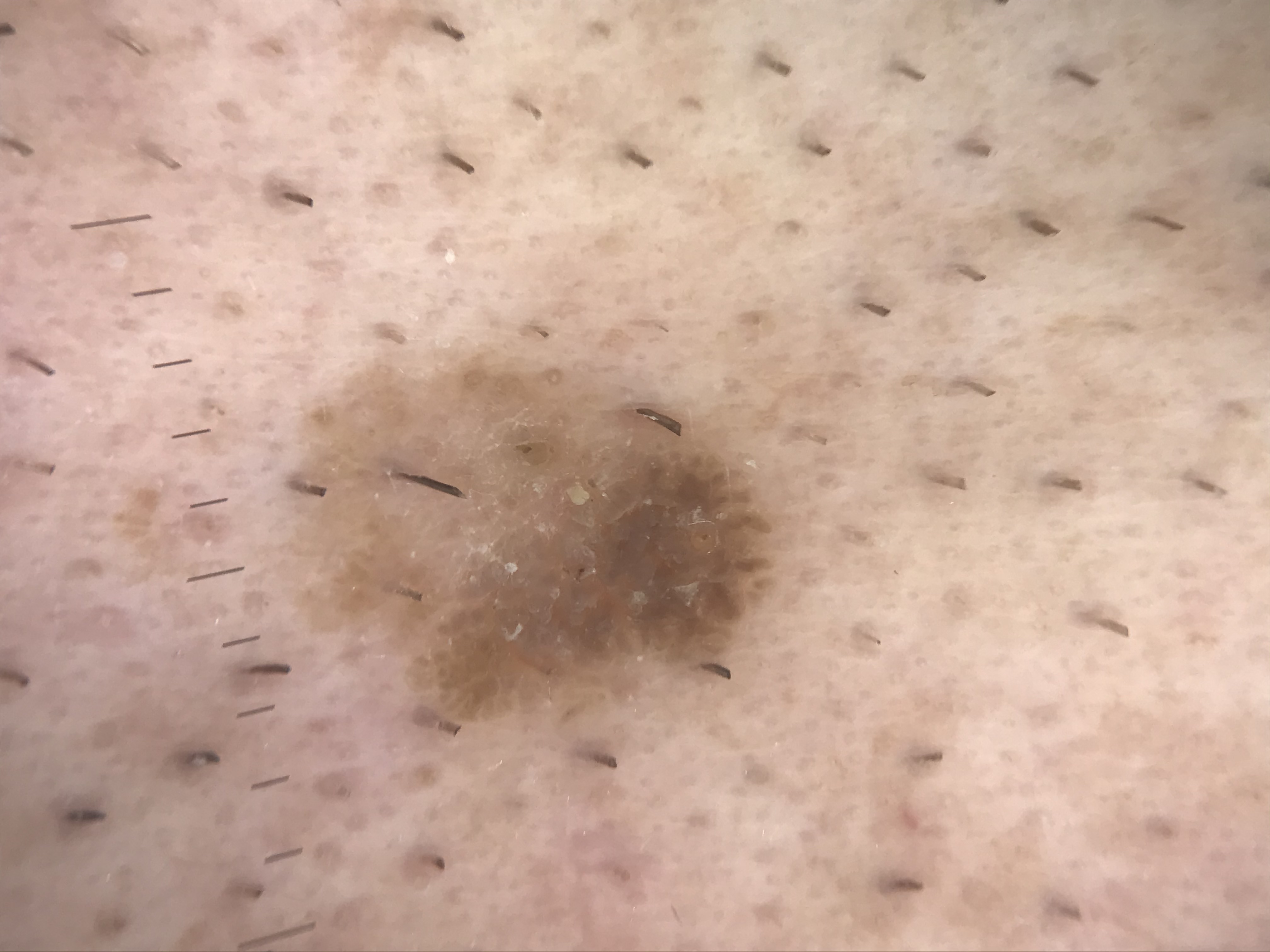The diagnostic label was a seborrheic keratosis.